A dermoscopic close-up of a skin lesion: 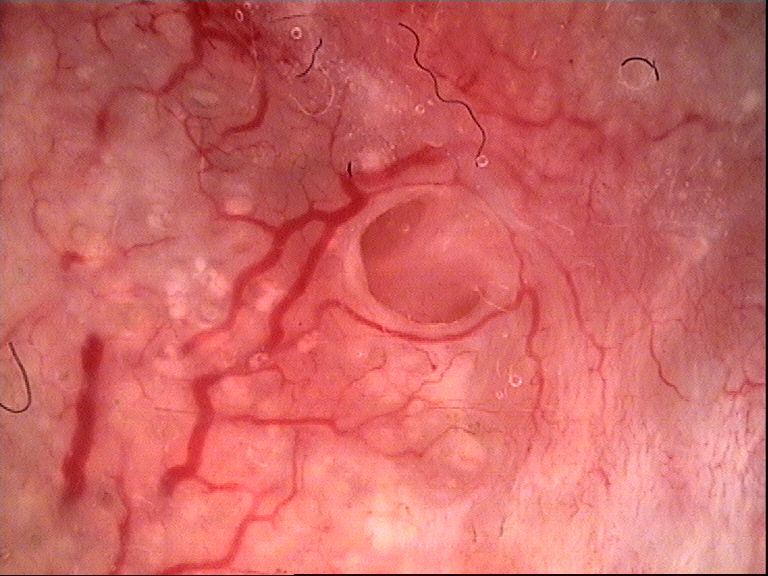diagnosis: basal cell carcinoma (biopsy-proven).